A male subject aged 68 · a clinical photograph showing a skin lesion · the patient is FST II — 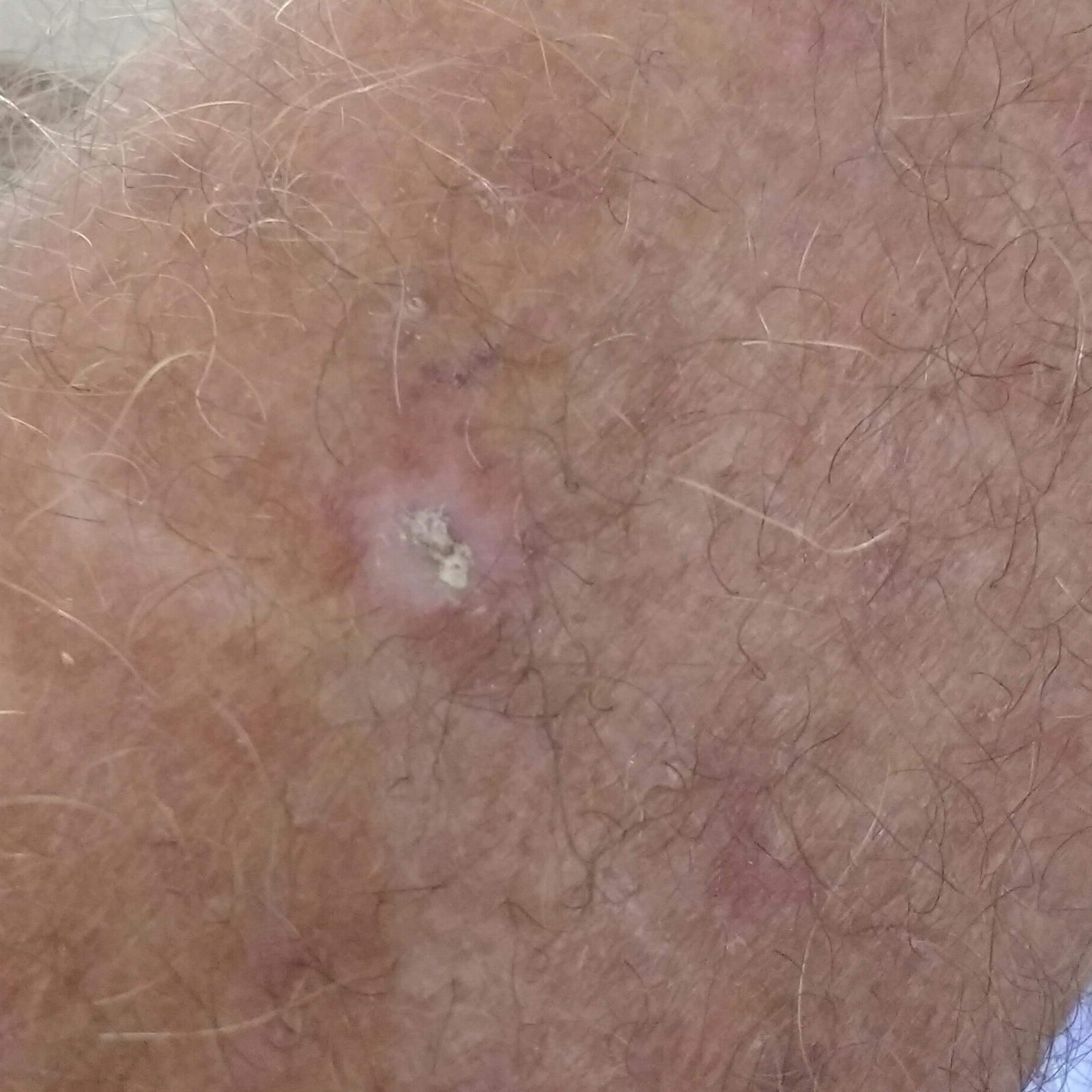{"lesion_location": "a forearm", "lesion_size": {"diameter_1_mm": 10.0, "diameter_2_mm": 10.0}, "symptoms": {"present": ["itching", "elevation", "growth", "bleeding"]}, "diagnosis": {"name": "actinic keratosis", "code": "ACK", "malignancy": "indeterminate", "confirmation": "histopathology"}}